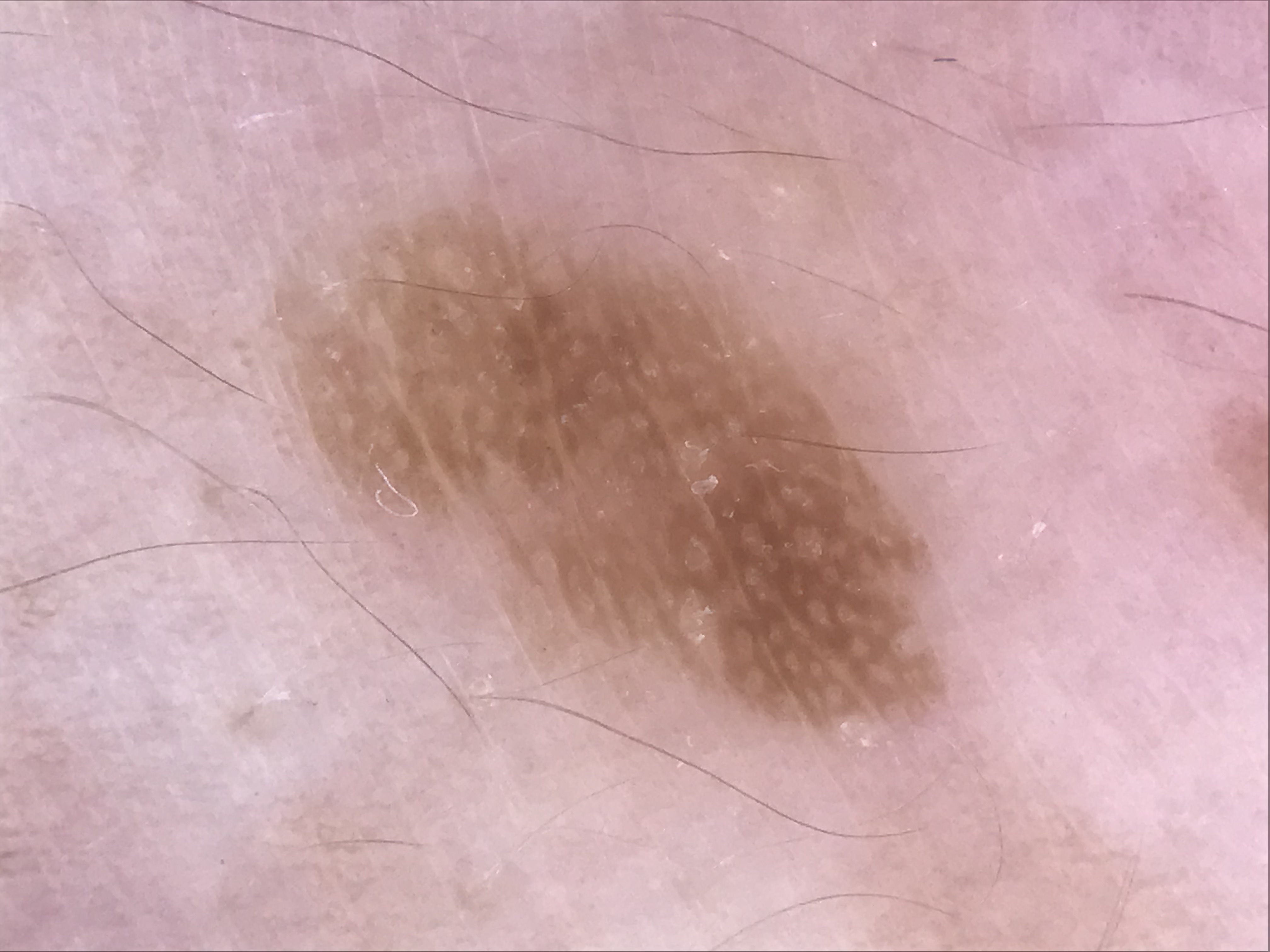class: seborrheic keratosis (expert consensus)